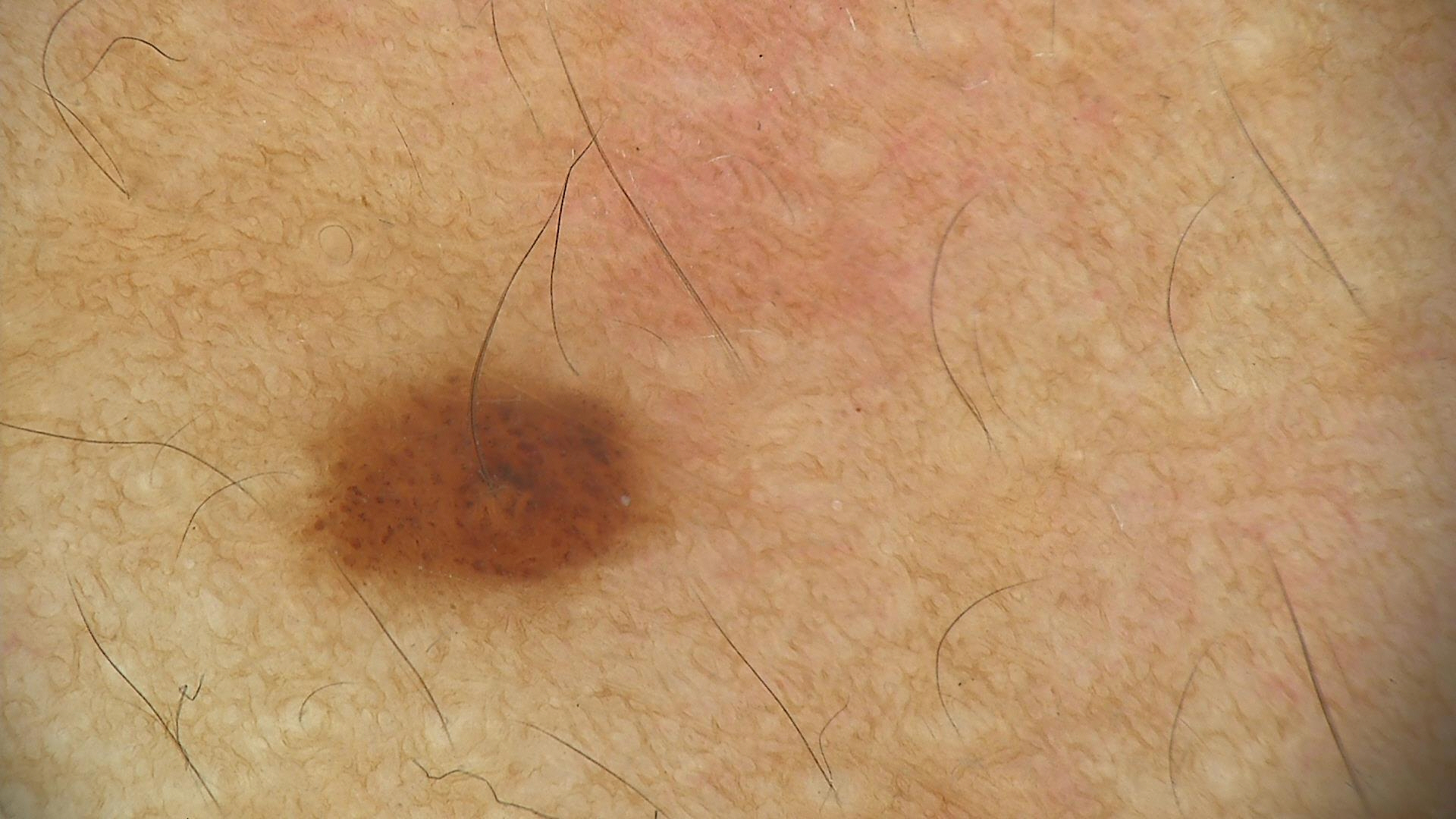A skin lesion imaged with a dermatoscope.
The diagnostic label was a benign lesion — a dysplastic junctional nevus.